The patient considered this a rash. The arm is involved. The photograph is a close-up of the affected area. Present for less than one week. Reported lesion symptoms include itching. No relevant systemic symptoms. Skin tone: Fitzpatrick phototype IV; human graders estimated MST 4: 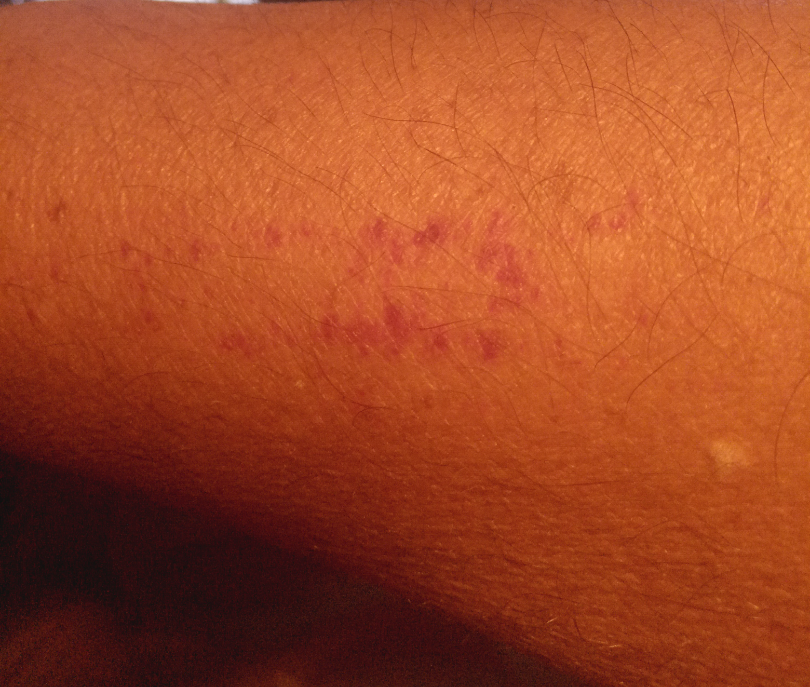The skin findings could not be characterized from the image.